A dermoscopic close-up of a skin lesion:
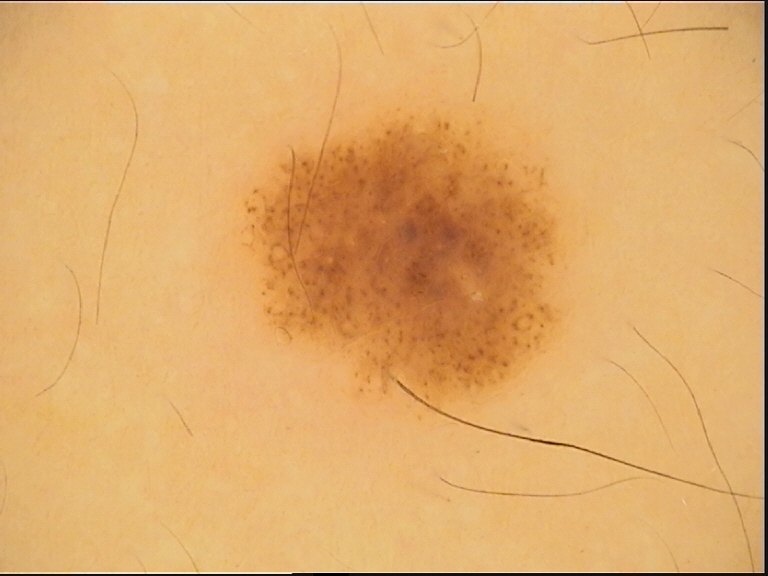{"diagnosis": {"name": "dysplastic junctional nevus", "code": "jd", "malignancy": "benign", "super_class": "melanocytic", "confirmation": "expert consensus"}}